Dermoscopy of a skin lesion; a male subject aged 48-52: 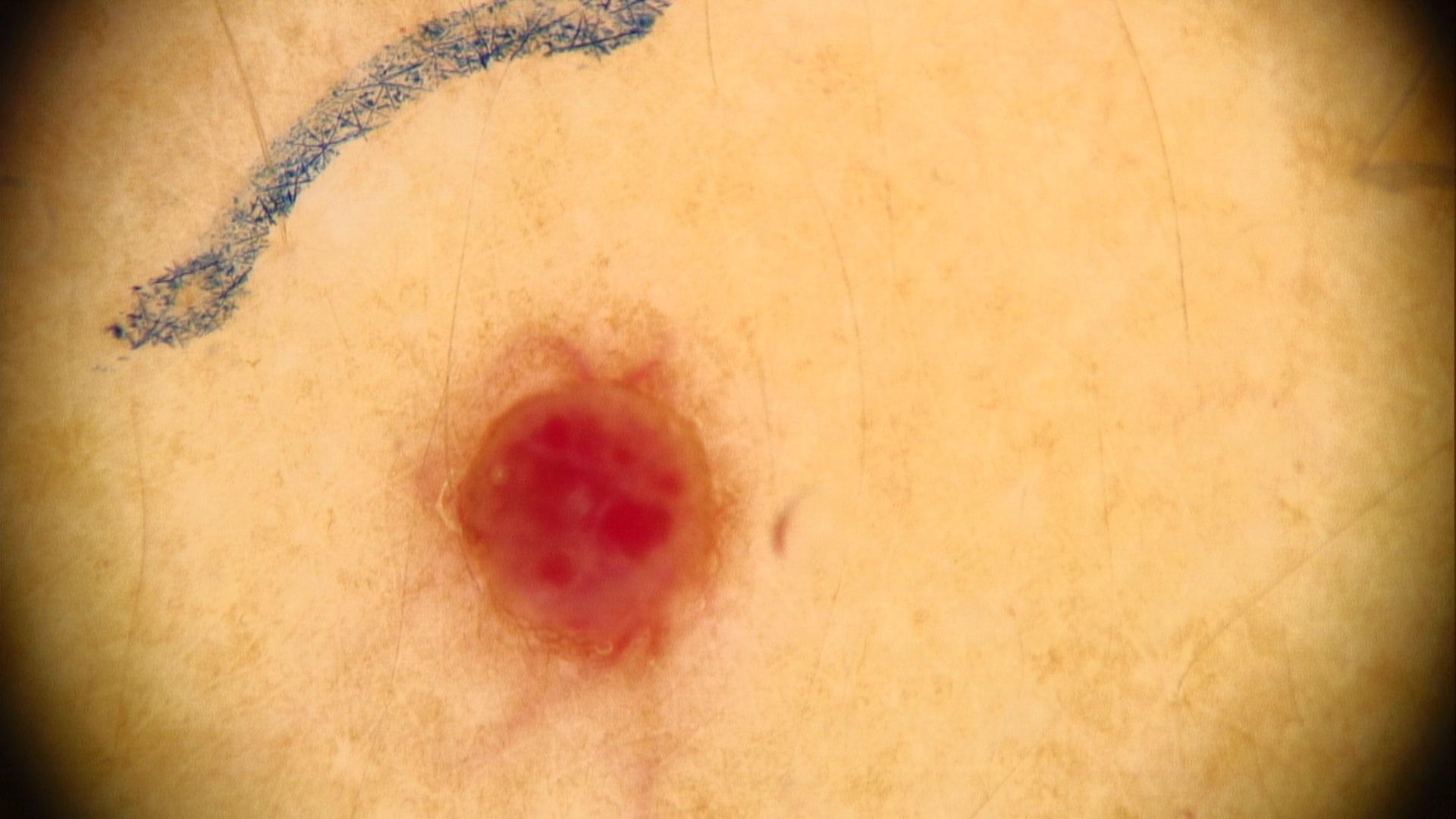anatomic site = the posterior trunk
diagnosis = vascular lesion (clinical impression)